The patient says their skin reddens with sun exposure; dermoscopy of a skin lesion; collected as part of a research study, without a referral diagnosis; a moderate number of moles by the patient's own estimate: 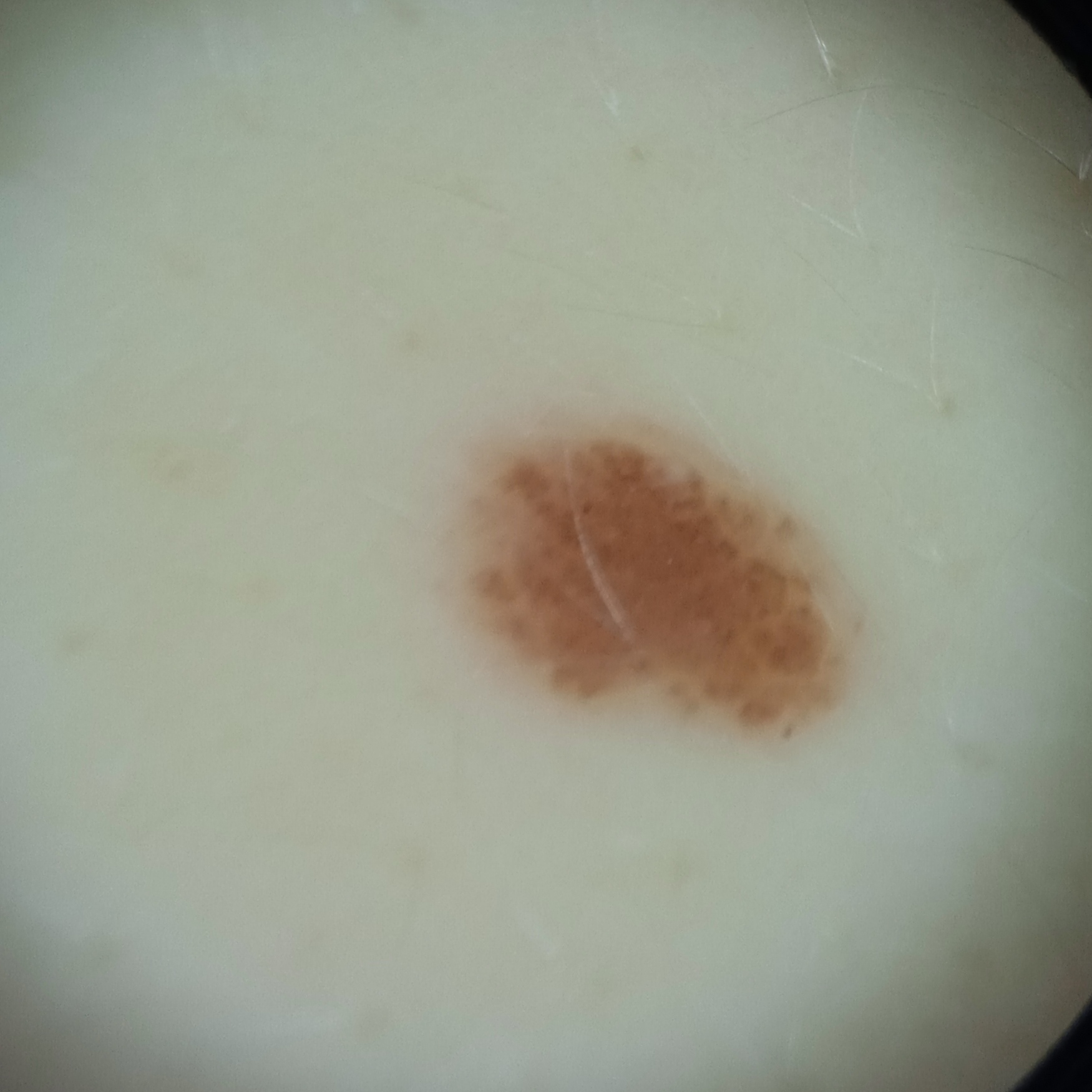| feature | finding |
|---|---|
| body site | the torso |
| diameter | 5.1 mm |
| diagnostic label | melanocytic nevus (dermatologist consensus) |